The patient was assessed as Fitzpatrick phototype II · a dermoscopic photograph of a skin lesion · a male subject aged approximately 80:
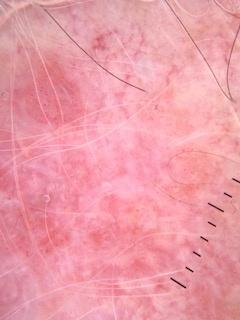anatomic site: the head or neck, diagnostic label: Squamous cell carcinoma (biopsy-proven).